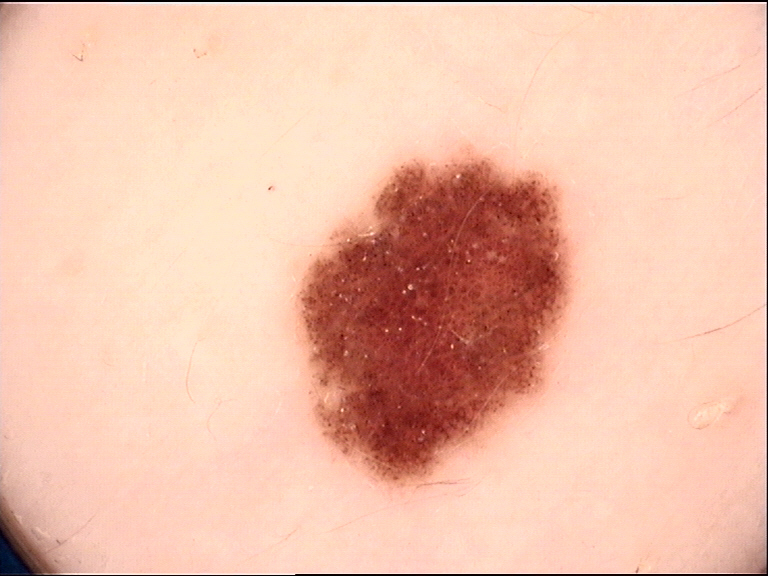diagnostic label — dysplastic junctional nevus (expert consensus)